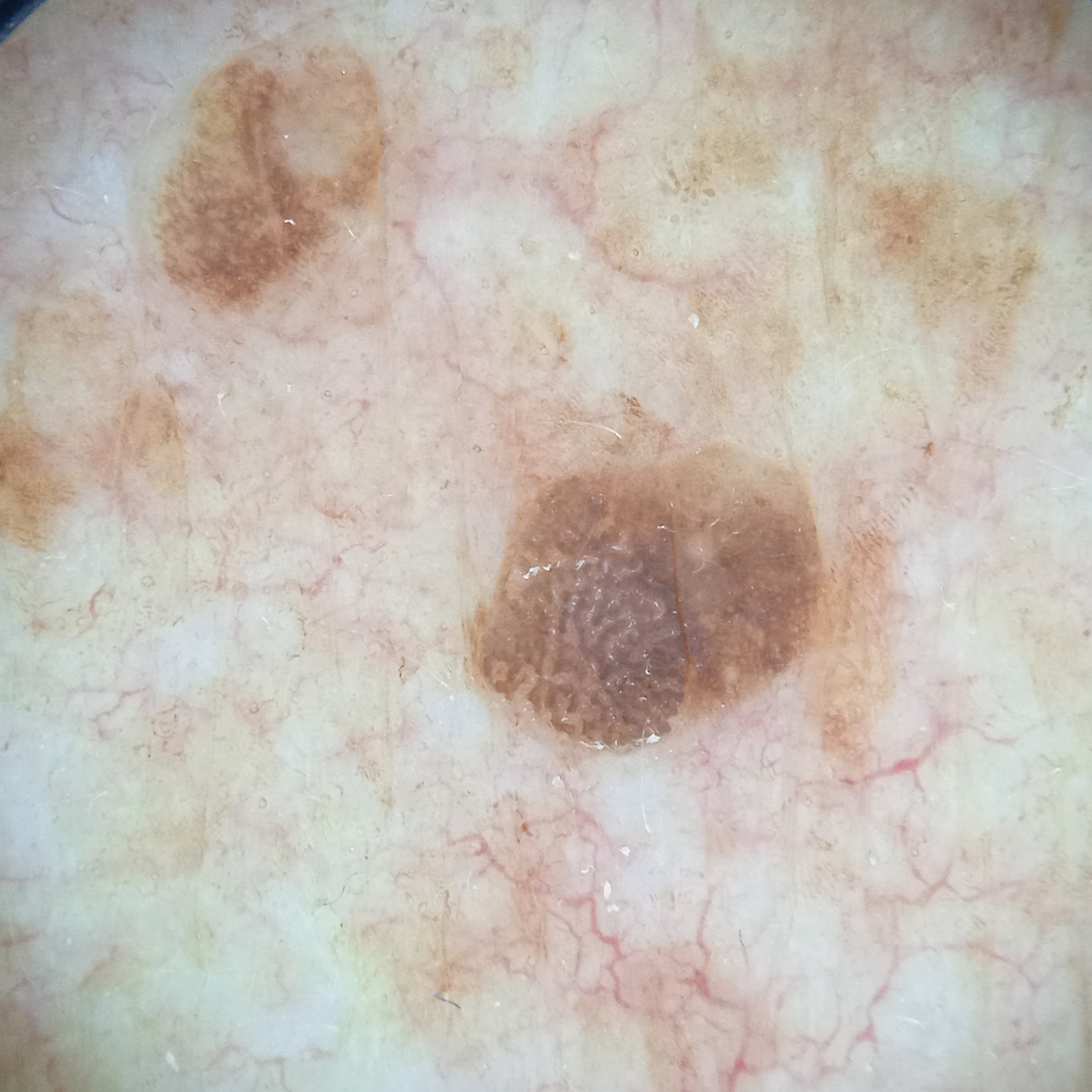<skin_lesion>
<referral>research study (no referral diagnosis)</referral>
<sun_reaction>skin tans without first burning</sun_reaction>
<risk_factors>
<positive>a personal history of cancer</positive>
</risk_factors>
<lesion_size>
<diameter_mm>4.6</diameter_mm>
</lesion_size>
<diagnosis>
<name>seborrheic keratosis</name>
<malignancy>benign</malignancy>
</diagnosis>
</skin_lesion>